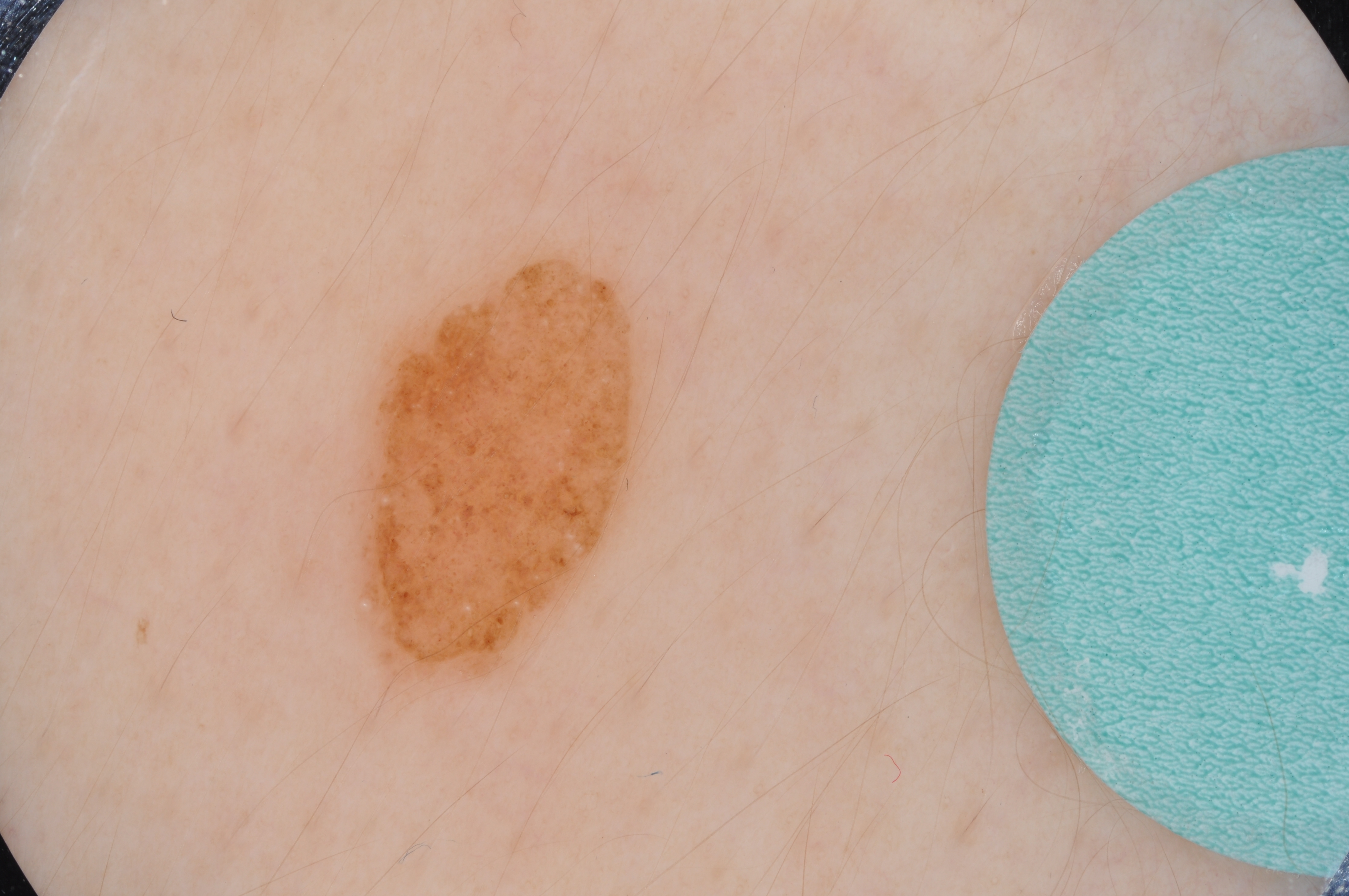| key | value |
|---|---|
| modality | dermoscopic image |
| dermoscopic features | milia-like cysts and globules |
| lesion size | moderate |
| bounding box | left=341, top=245, right=663, bottom=705 |
| diagnostic label | a melanocytic nevus, a benign skin lesion |